A subject age 6: 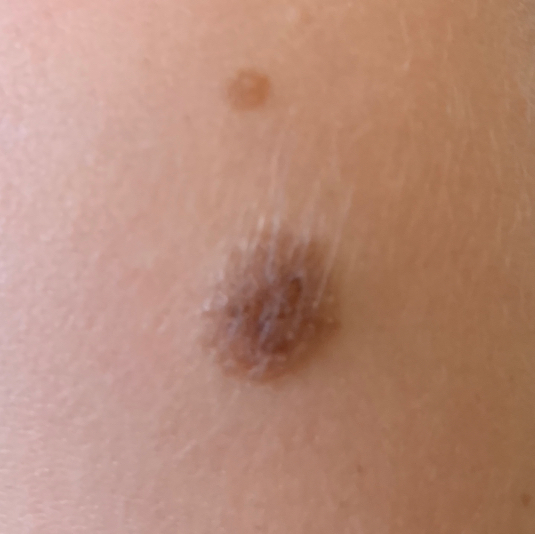Clinical context:
Located on an arm.
Conclusion:
The clinical impression was a nevus.